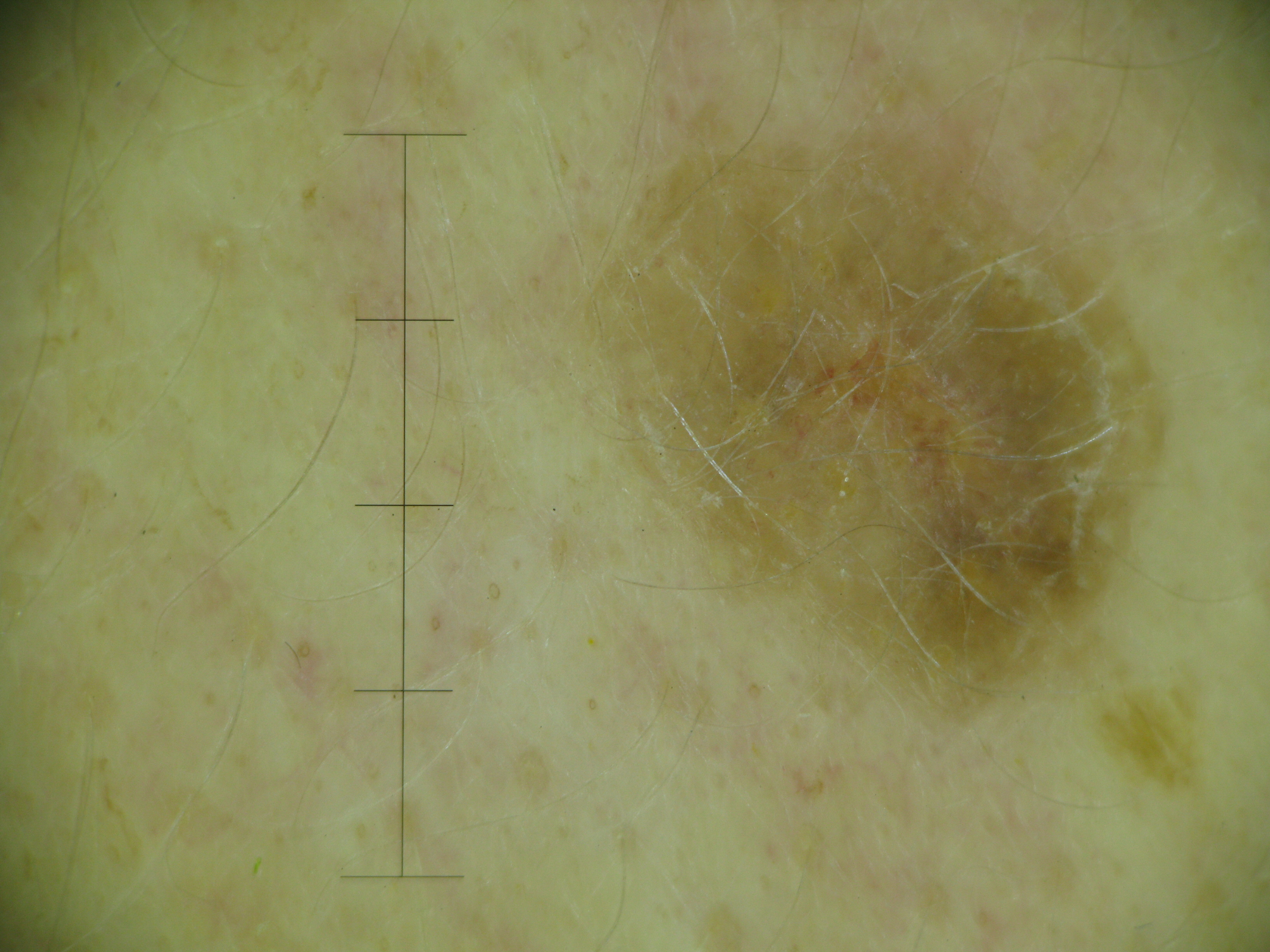The architecture is that of a keratinocytic lesion. The diagnosis was a benign lesion — a seborrheic keratosis.